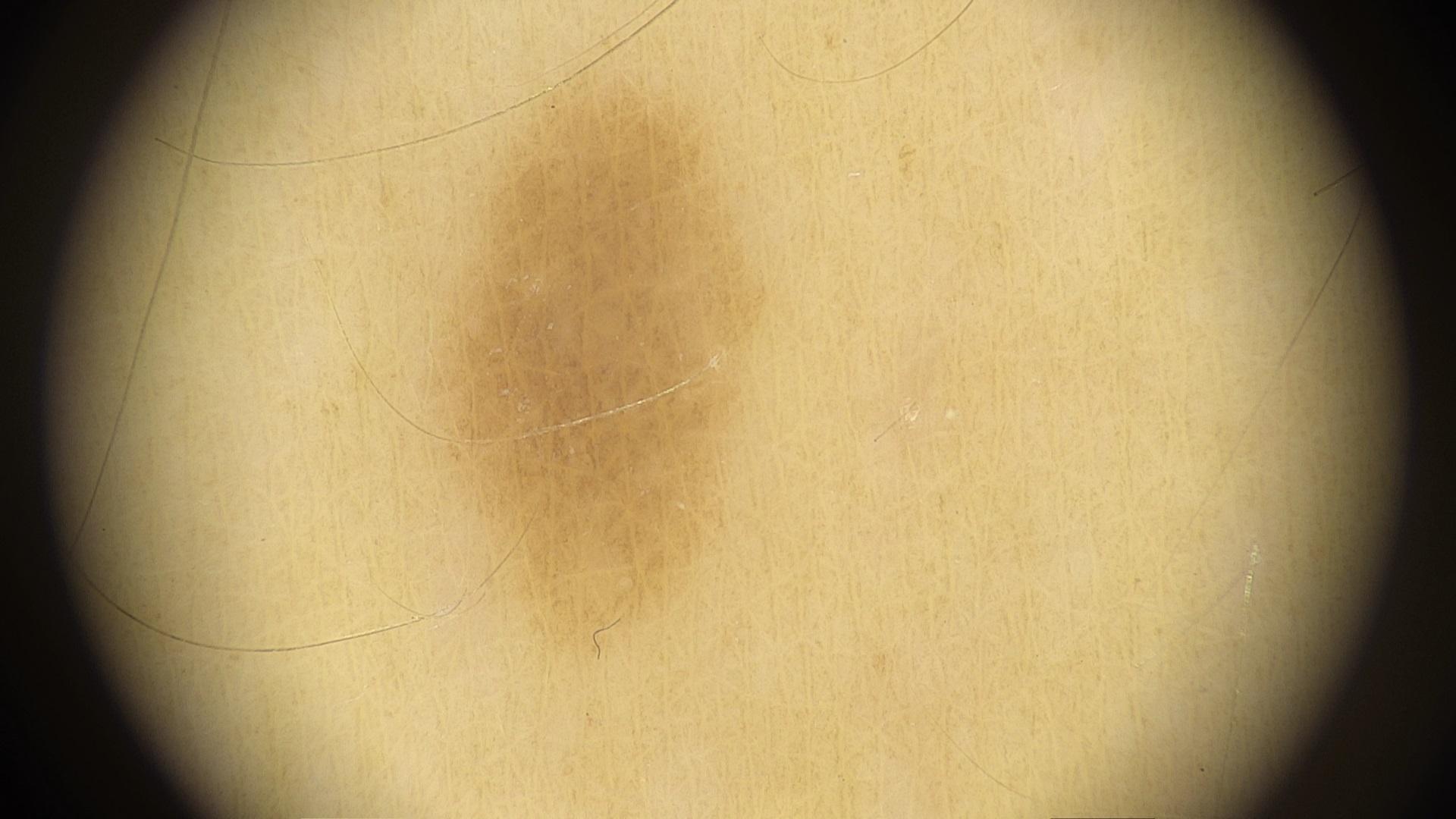The clinical impression was a nevus.